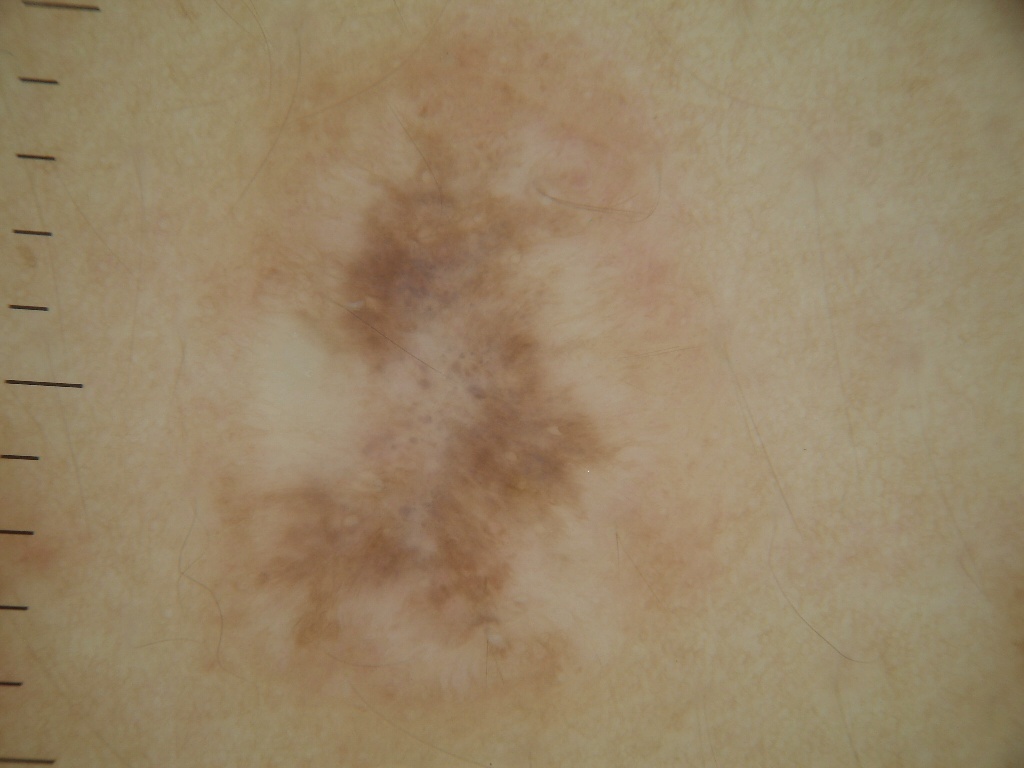Findings: A dermoscopic view of a skin lesion. The lesion takes up about 34% of the image. The lesion spans x1=204 y1=32 x2=673 y2=707. Conclusion: Consistent with a benign skin lesion.